The photograph was taken at a distance; the lesion is associated with bothersome appearance and itching; the affected area is the head or neck; skin tone: Fitzpatrick phototype II; associated systemic symptoms include joint pain; the contributor is 18–29, female; the contributor reports the condition has been present for about one day.
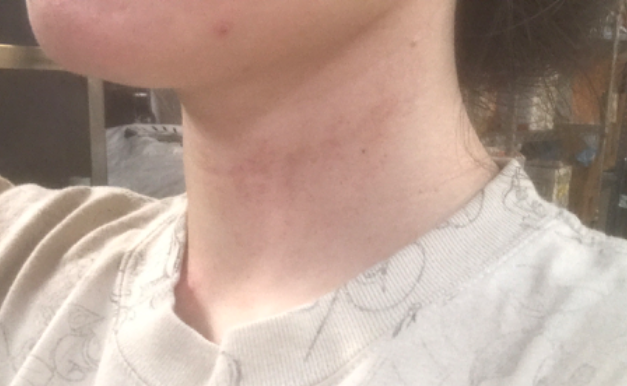The differential is split between Allergic Contact Dermatitis and Irritant Contact Dermatitis.